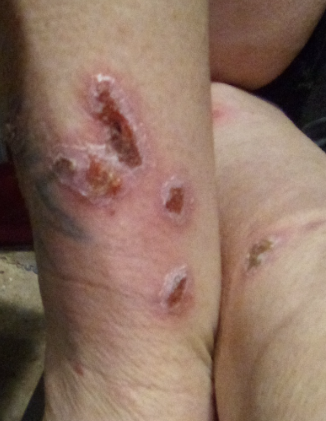Notes:
– assessment · indeterminate from the photograph
– shot type · close-up